Located on the arm. The contributor is a female aged 30–39. A close-up photograph: 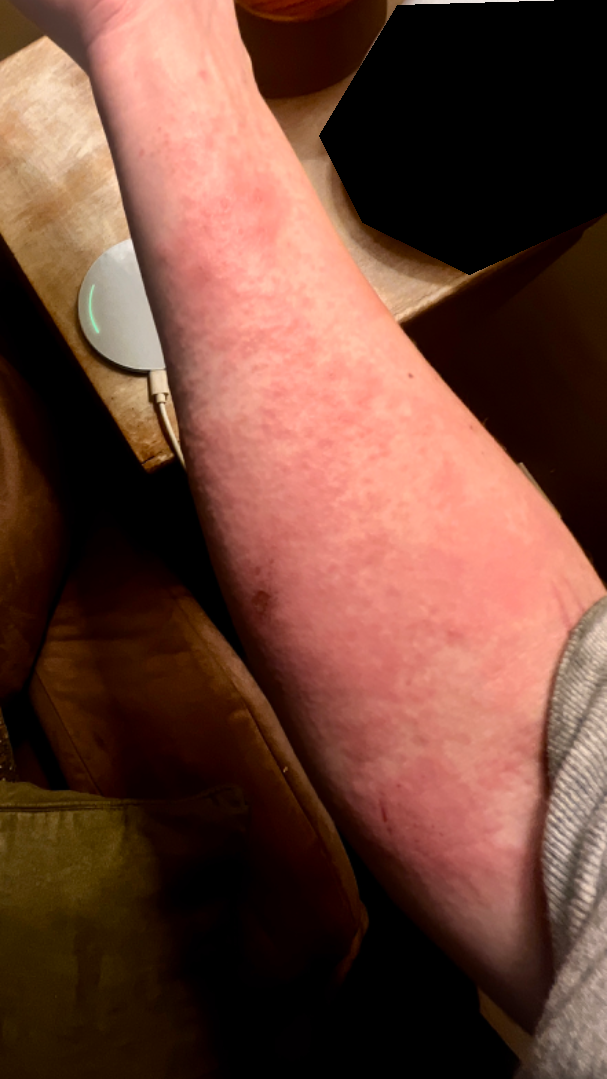The dermatologist could not determine a likely condition from the photograph alone.
The patient also reports fatigue.
The lesion is described as rough or flaky, raised or bumpy and fluid-filled.
Reported duration is one to four weeks.